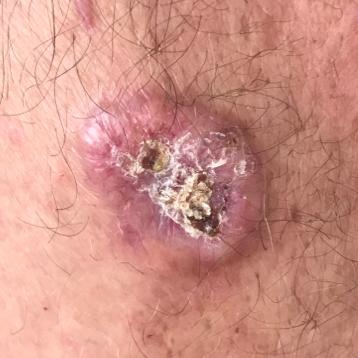A clinical photograph showing a skin lesion.
The patient is Fitzpatrick phototype II.
A male subject aged 64.
On biopsy, the diagnosis was a basal cell carcinoma.